The photograph is a close-up of the affected area.
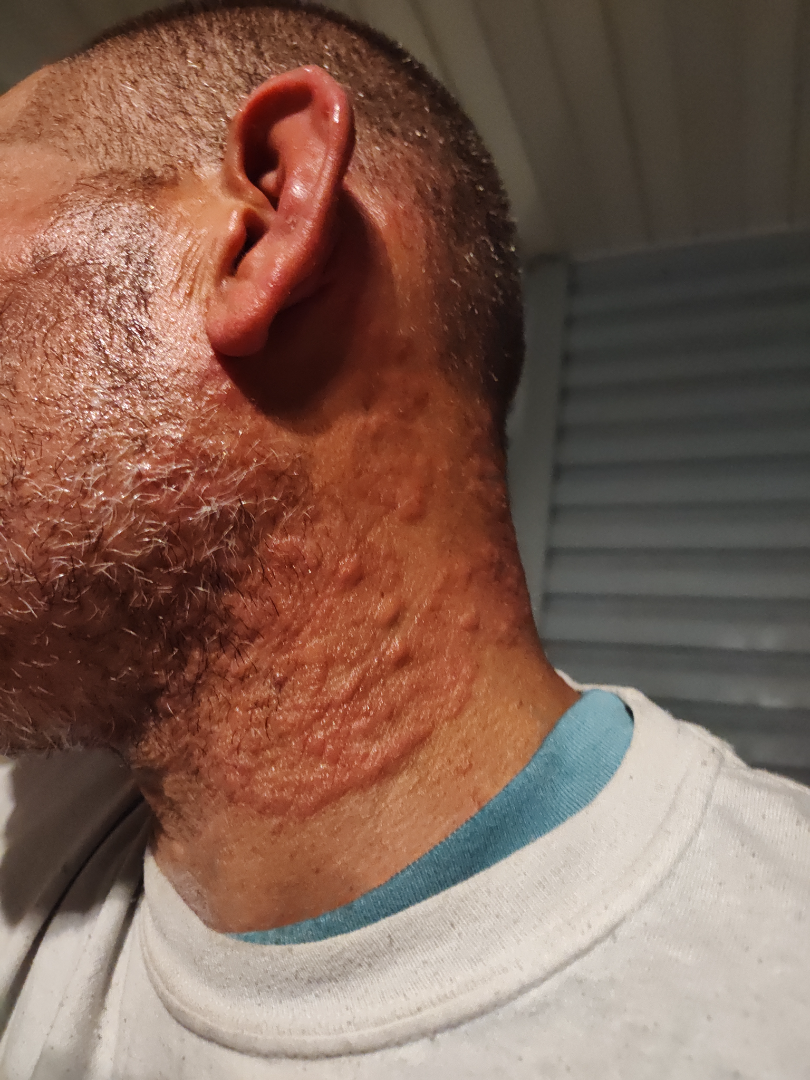Assessment:
On photographic review by a dermatologist: favoring Granuloma annulare; possibly Cutaneous sarcoidosis; lower on the differential is Erythema annulare centrifugum.